A dermoscopic photograph of a skin lesion.
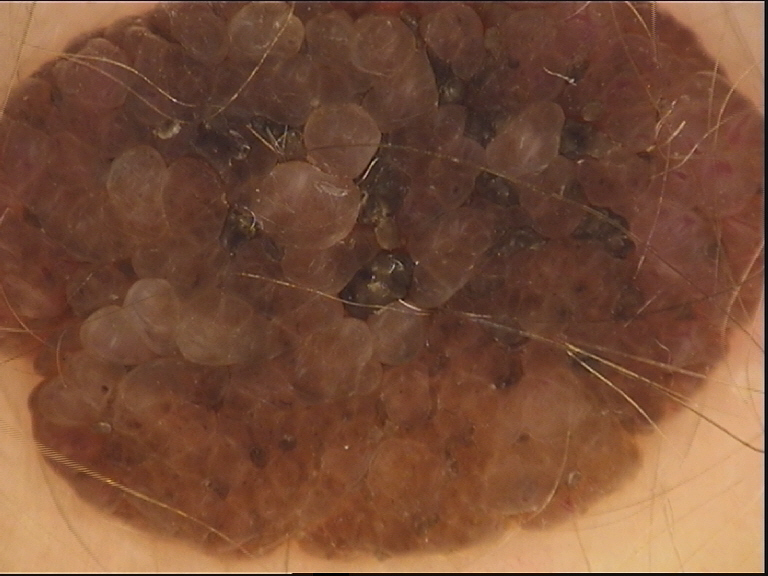Findings:
– category · banal
– diagnostic label · dermal nevus (expert consensus)